A skin lesion imaged with a dermatoscope.
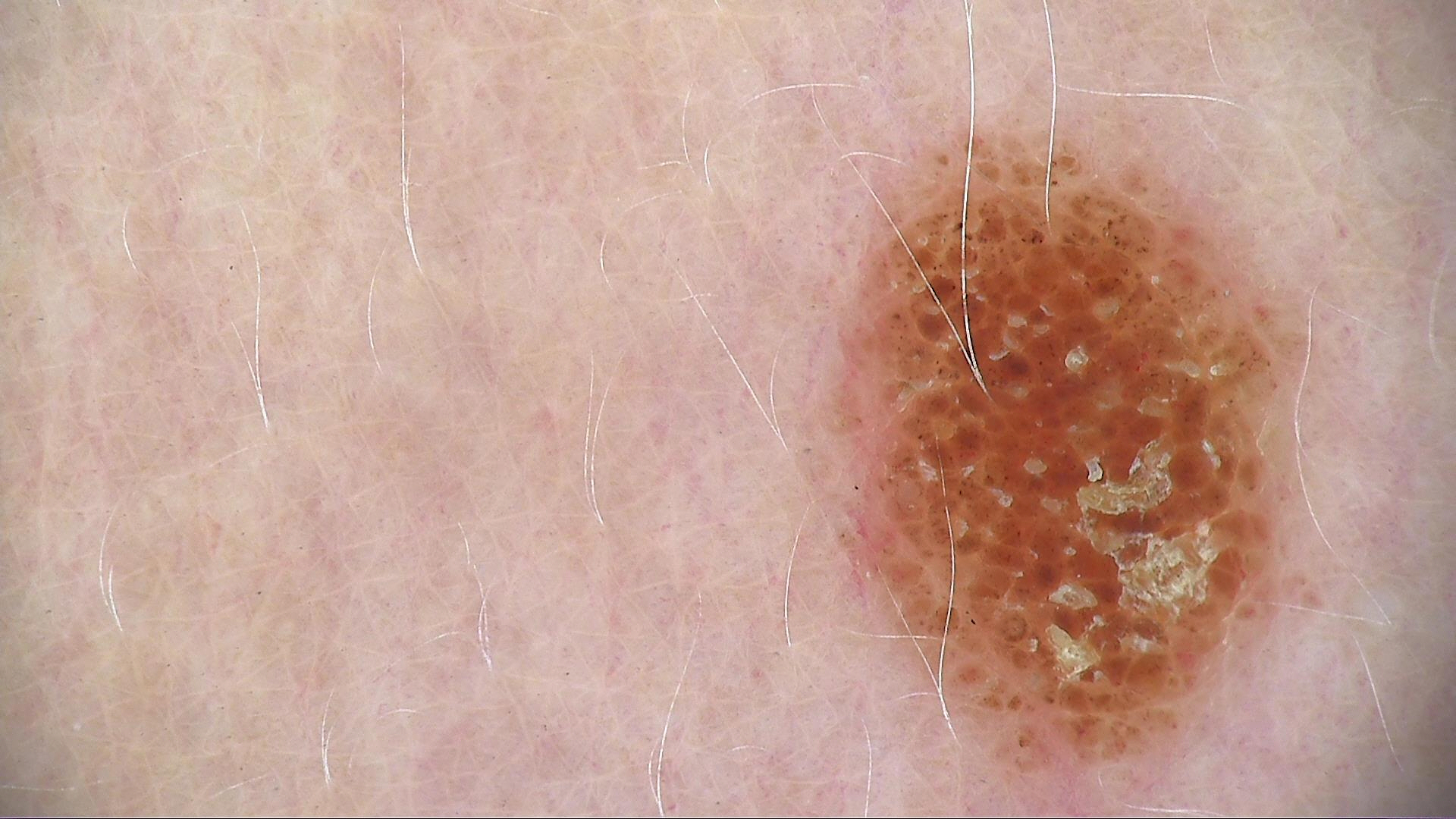The diagnostic label was a banal lesion — a compound nevus.